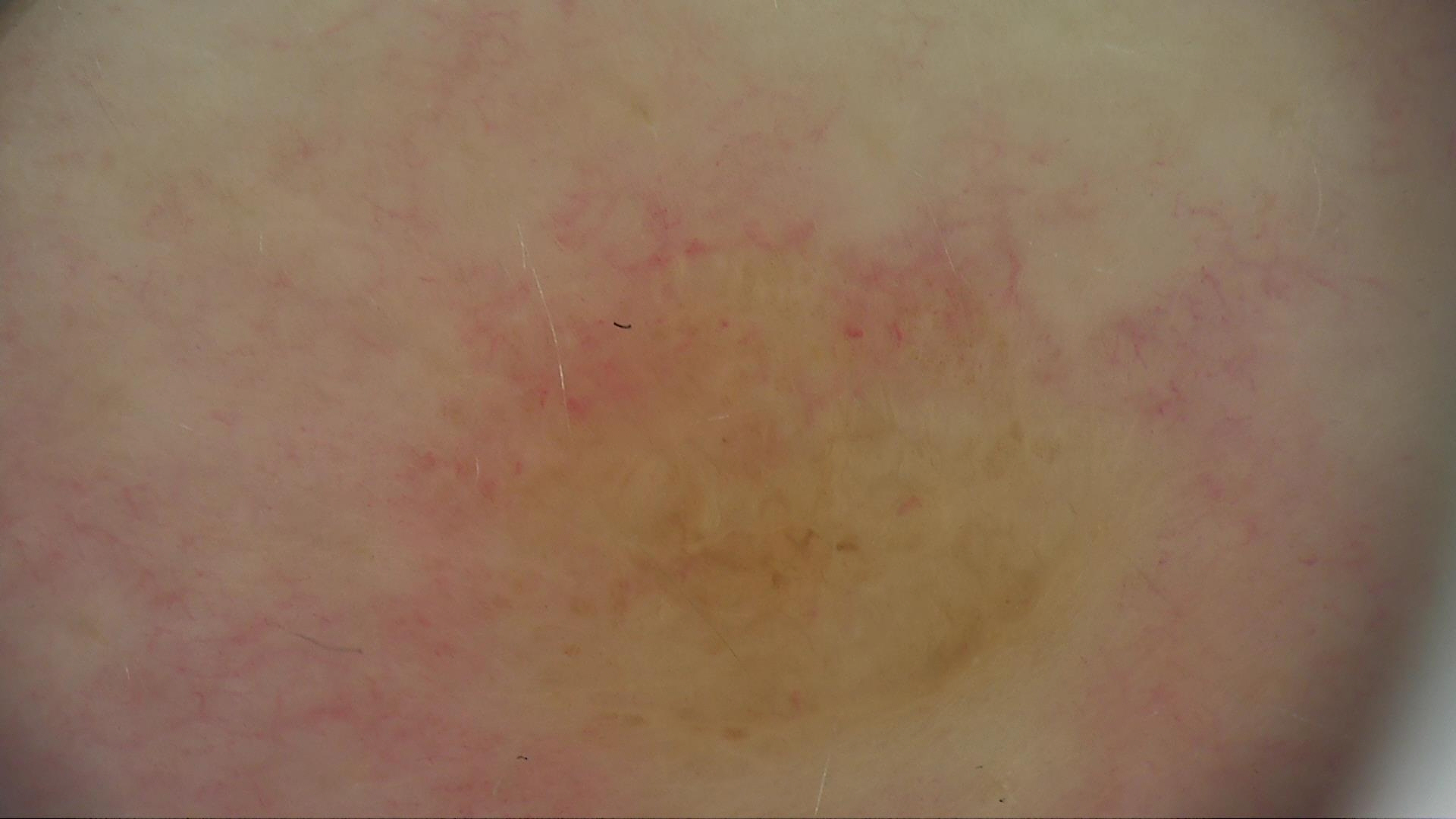Case:
A dermoscopy image of a single skin lesion. The architecture is that of a banal lesion.
Conclusion:
The diagnosis was a dermal nevus.